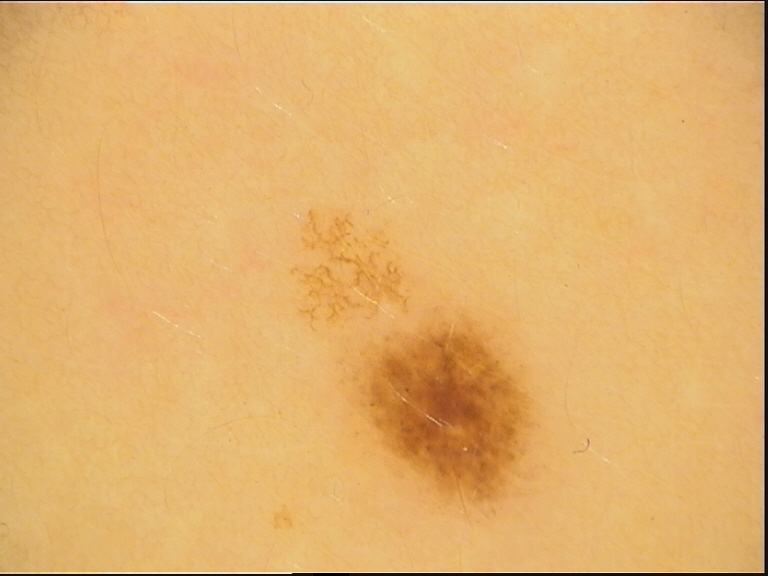modality = dermoscopy
assessment = dysplastic junctional nevus (expert consensus)